Dermoscopy of a skin lesion:
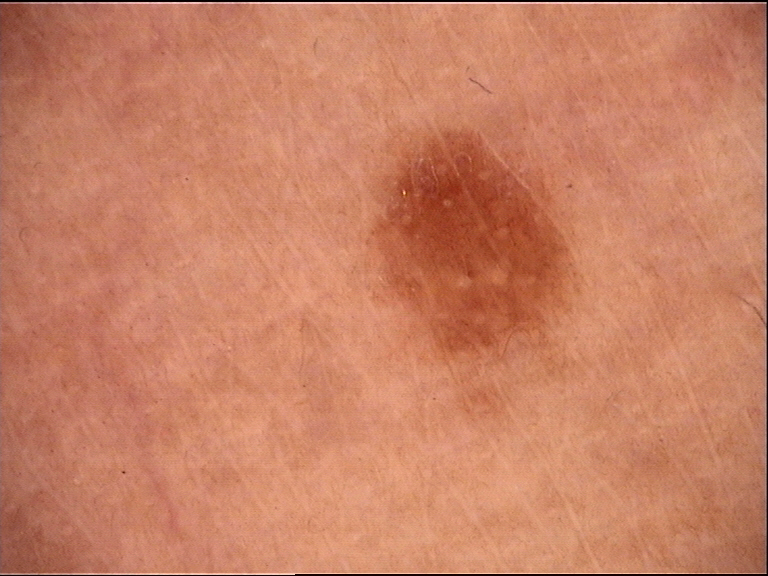Q: What was the diagnostic impression?
A: junctional nevus (expert consensus)